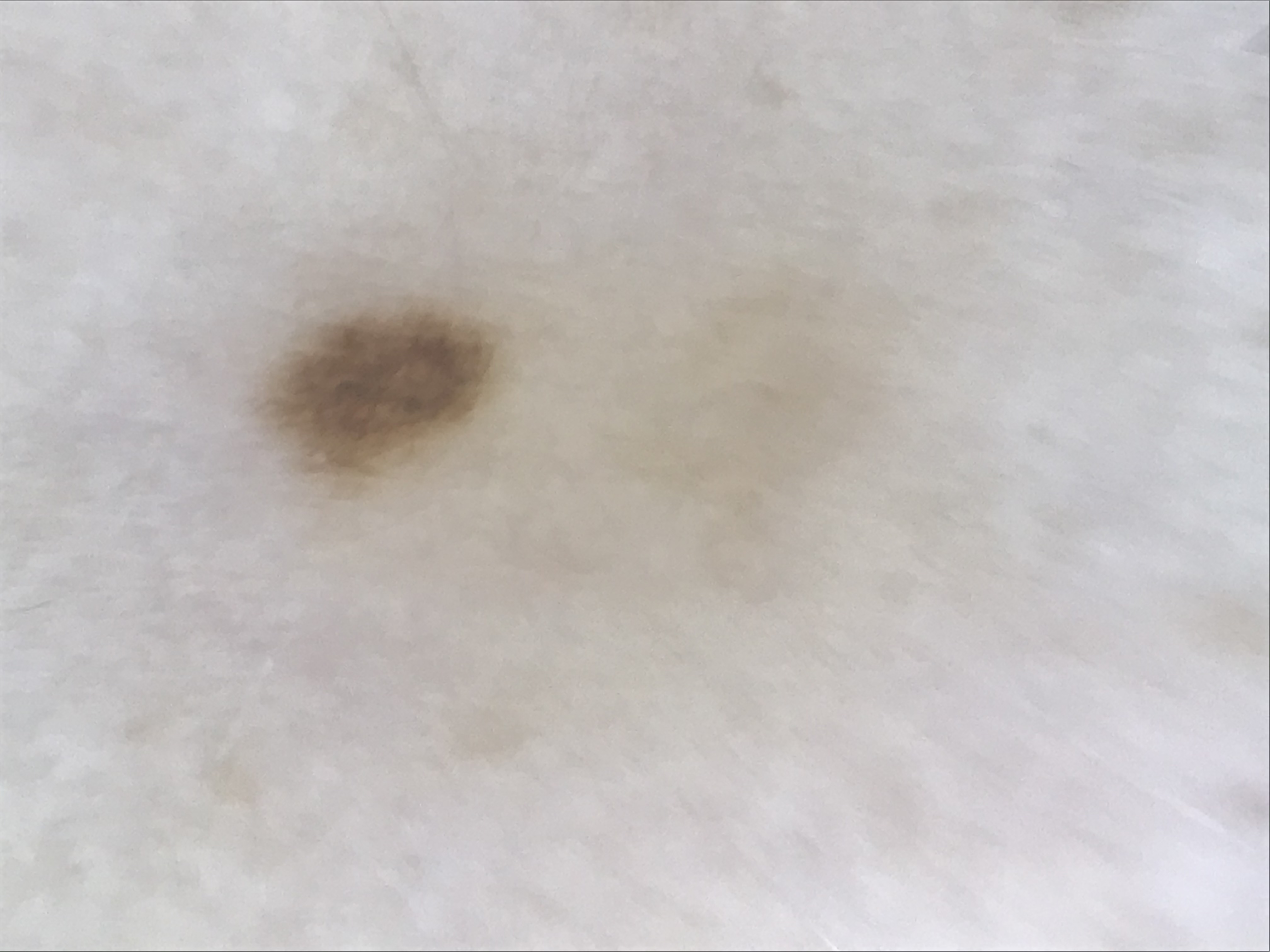| field | value |
|---|---|
| class | acral dysplastic junctional nevus (expert consensus) |